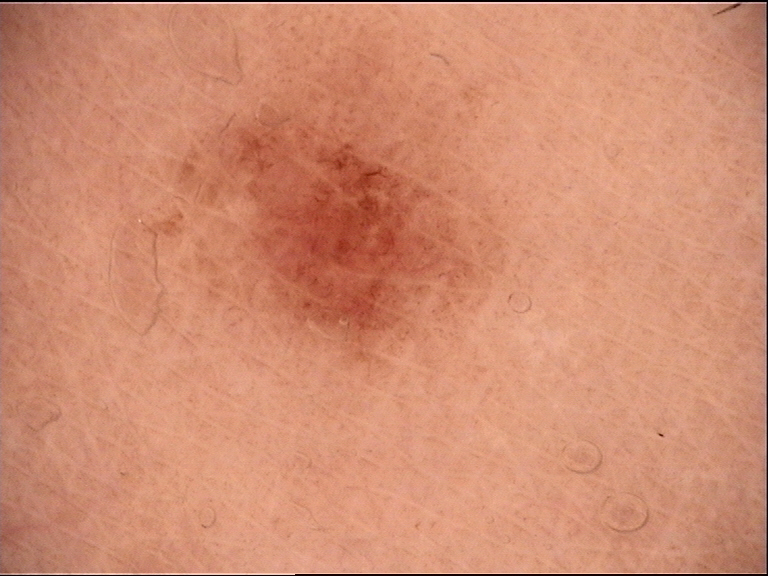The diagnostic label was a dysplastic junctional nevus.